The patient was assessed as Fitzpatrick II · a dermoscopic close-up of a skin lesion · a female patient aged 48 to 52 · per the chart, a previous melanoma but no melanoma in first-degree relatives: 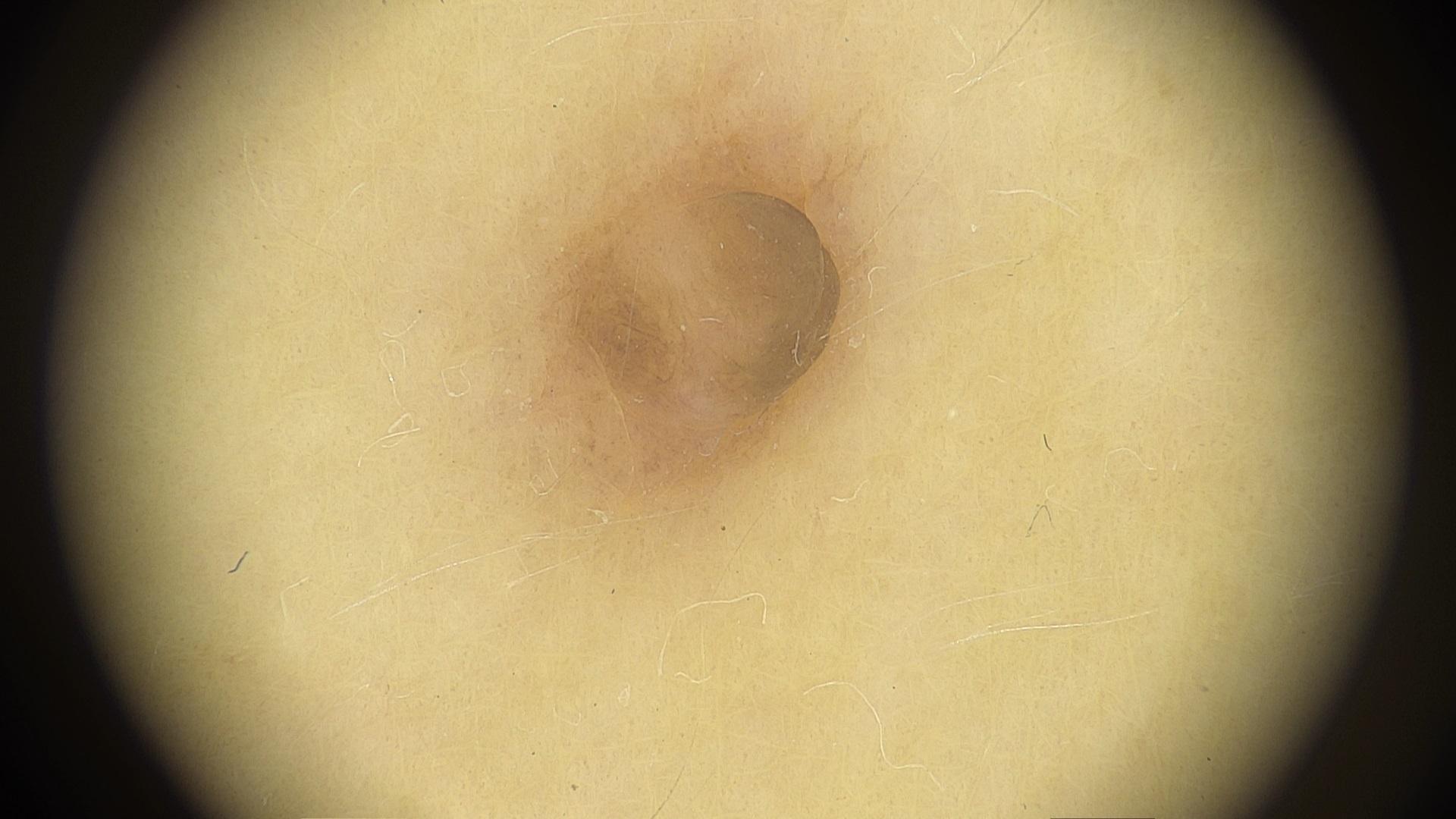site=the trunk (the anterior trunk) | assessment=Nevus.